This image was taken at an angle. The affected area is the leg and top or side of the foot. Female subject, age 30–39: 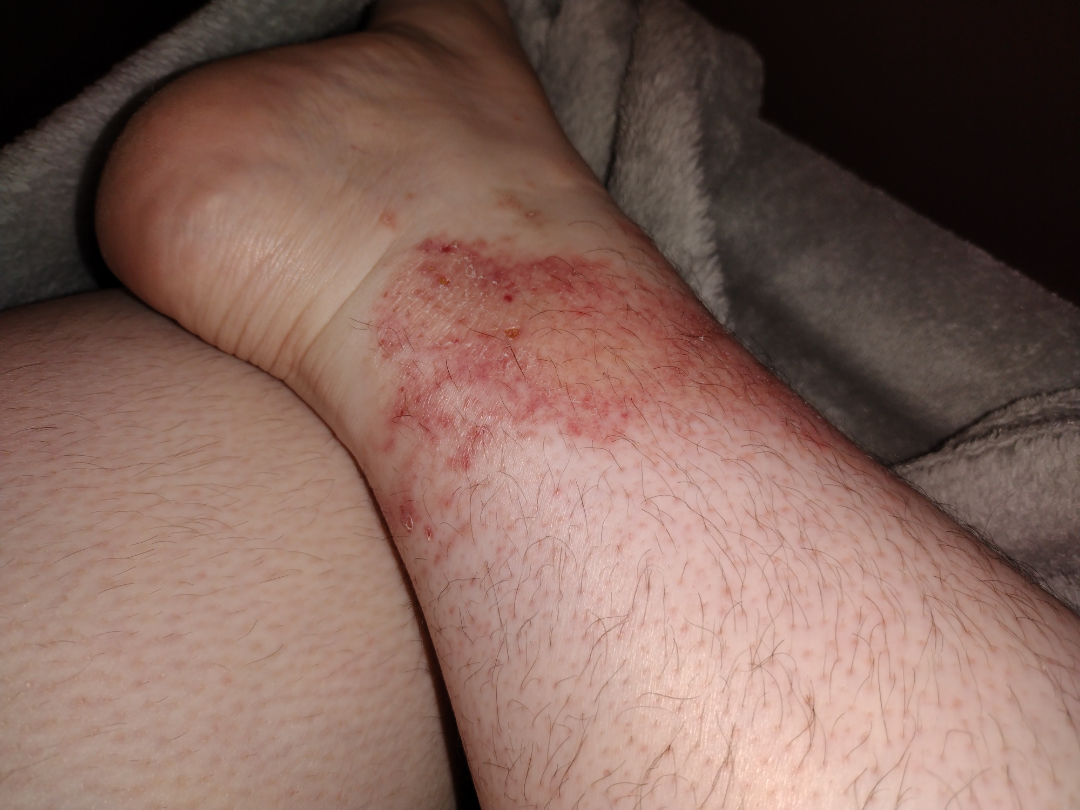history=one to four weeks
self-categorized as=a rash
symptoms=pain, itching, darkening, burning and enlargement
described texture=rough or flaky and raised or bumpy
impression=Allergic Contact Dermatitis (considered); Stasis Dermatitis (considered); Eczema (considered); Irritant Contact Dermatitis (remote); Contact dermatitis (remote)